A moderate number of moles by the patient's own estimate. Collected as part of a research study, without a referral diagnosis. The patient reports no personal history of cancer and no personal history of skin cancer. A dermoscopic image of a skin lesion — 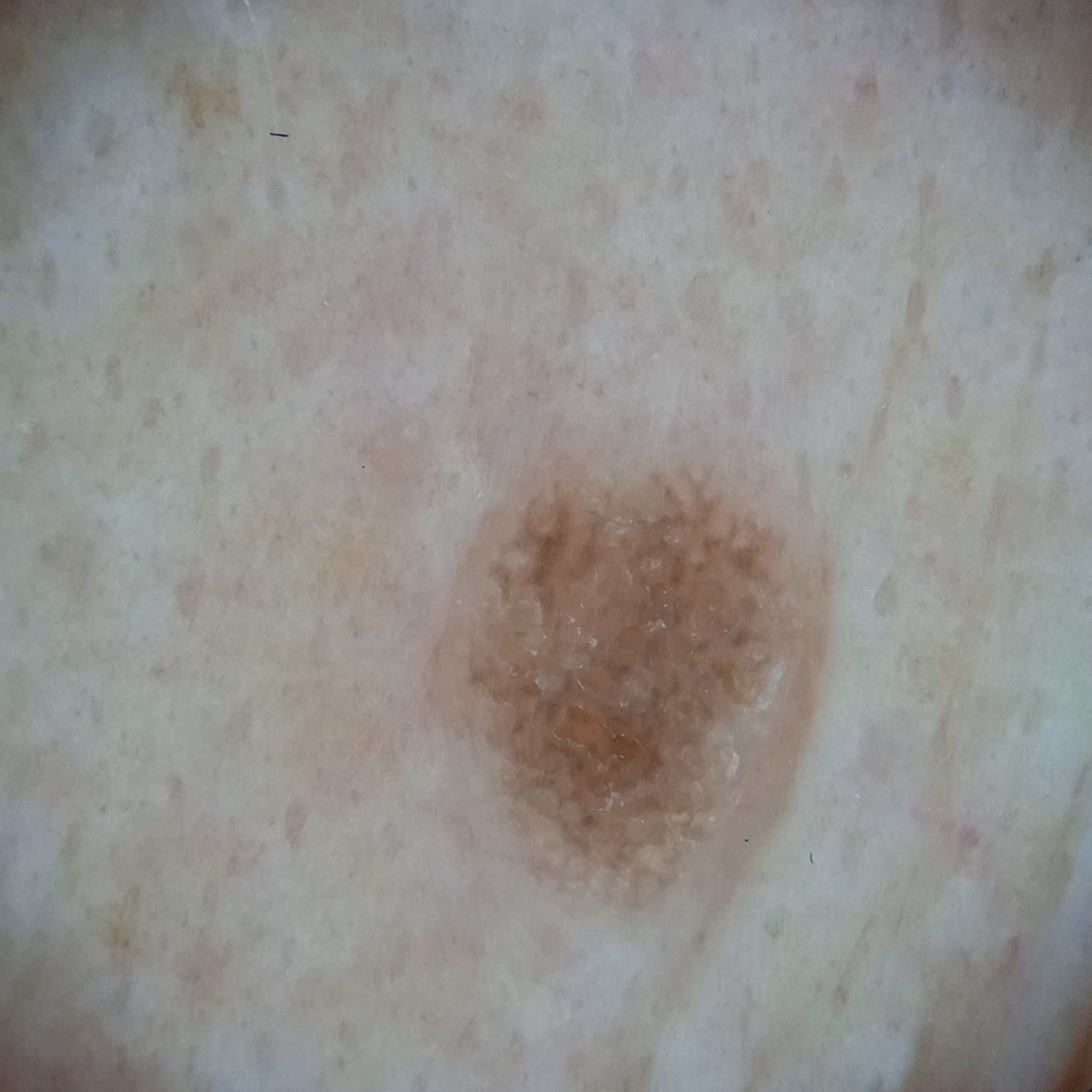Findings:
• location — the face
• lesion size — 5.3 mm
• diagnosis — seborrheic keratosis (dermatologist consensus)